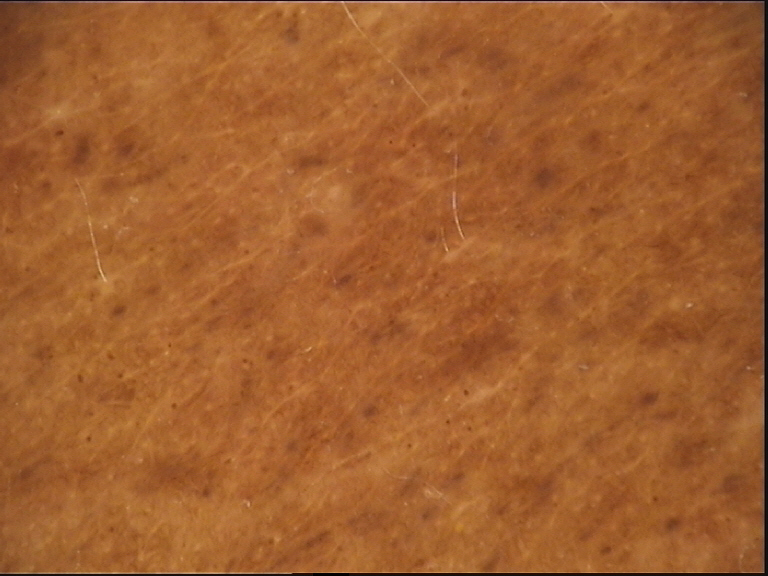| field | value |
|---|---|
| image | dermatoscopy |
| lesion type | banal |
| label | congenital compound nevus (expert consensus) |